An image taken at a distance; located on the arm, back of the torso, head or neck and front of the torso; the patient is 18–29, female: 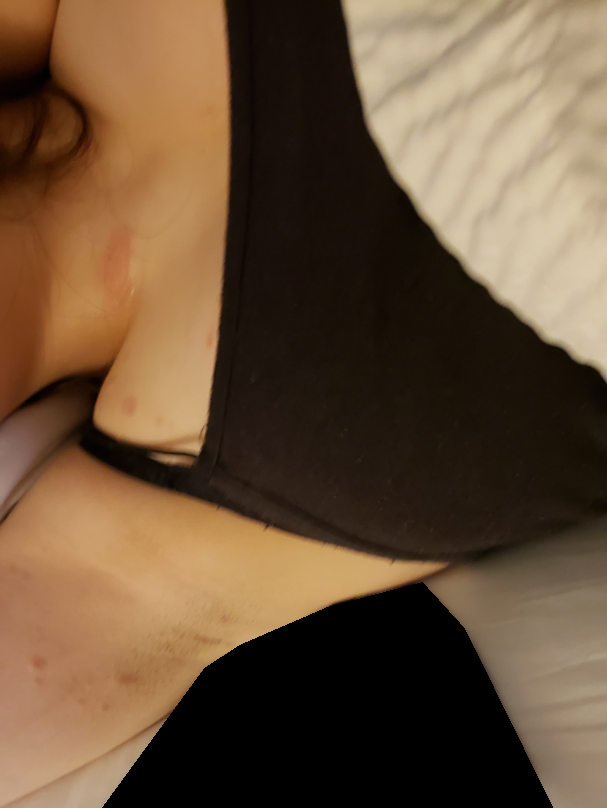Findings:
The dermatologist could not determine a likely condition from the photograph alone.
Background:
The patient considered this a rash. The lesion is described as raised or bumpy and rough or flaky. The contributor reports the condition has been present for less than one week. The contributor reports itching, bothersome appearance and enlargement.